A dermatoscopic image of a skin lesion.
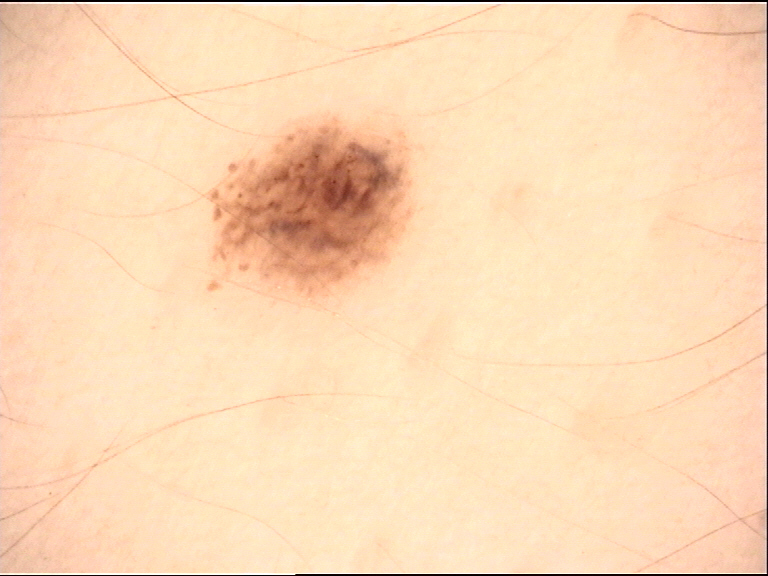The diagnosis was a banal lesion — a compound nevus.